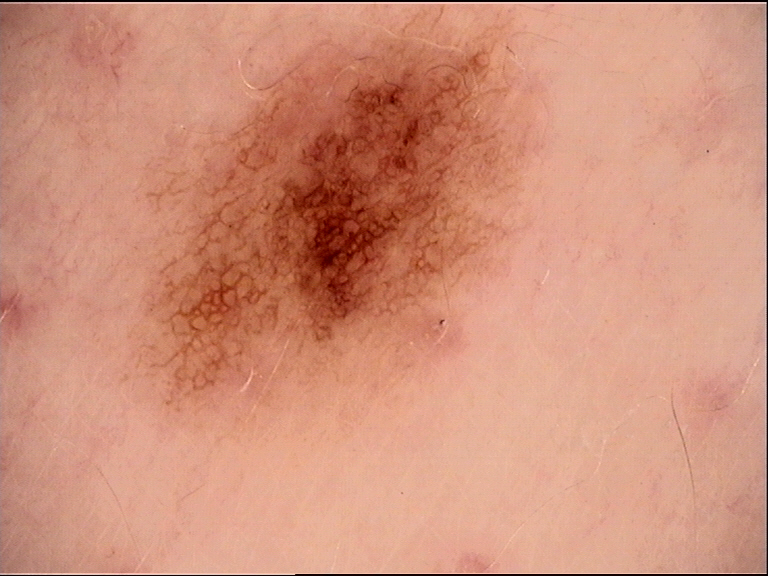label=dysplastic junctional nevus (expert consensus).